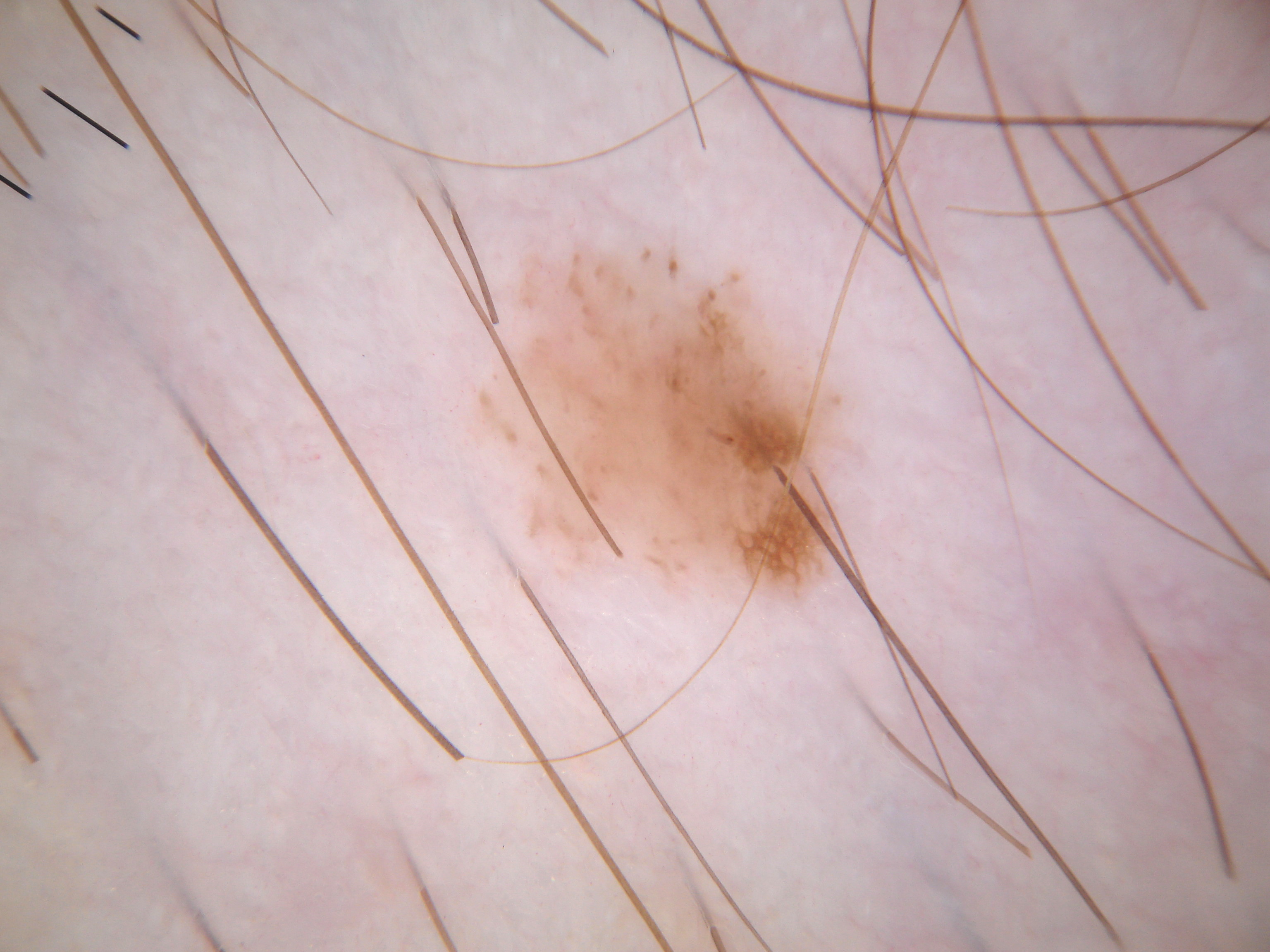A skin lesion imaged with a dermatoscope.
A moderately sized lesion.
The dermoscopic pattern shows pigment network and globules, with no streaks, negative network, or milia-like cysts.
The lesion is bounded by 457 224 856 627.
Diagnosed as a melanocytic nevus.